A clinical overview photograph of a skin lesion. The chart documents a prior melanoma. A female patient aged 68-72. The patient is skin type II.
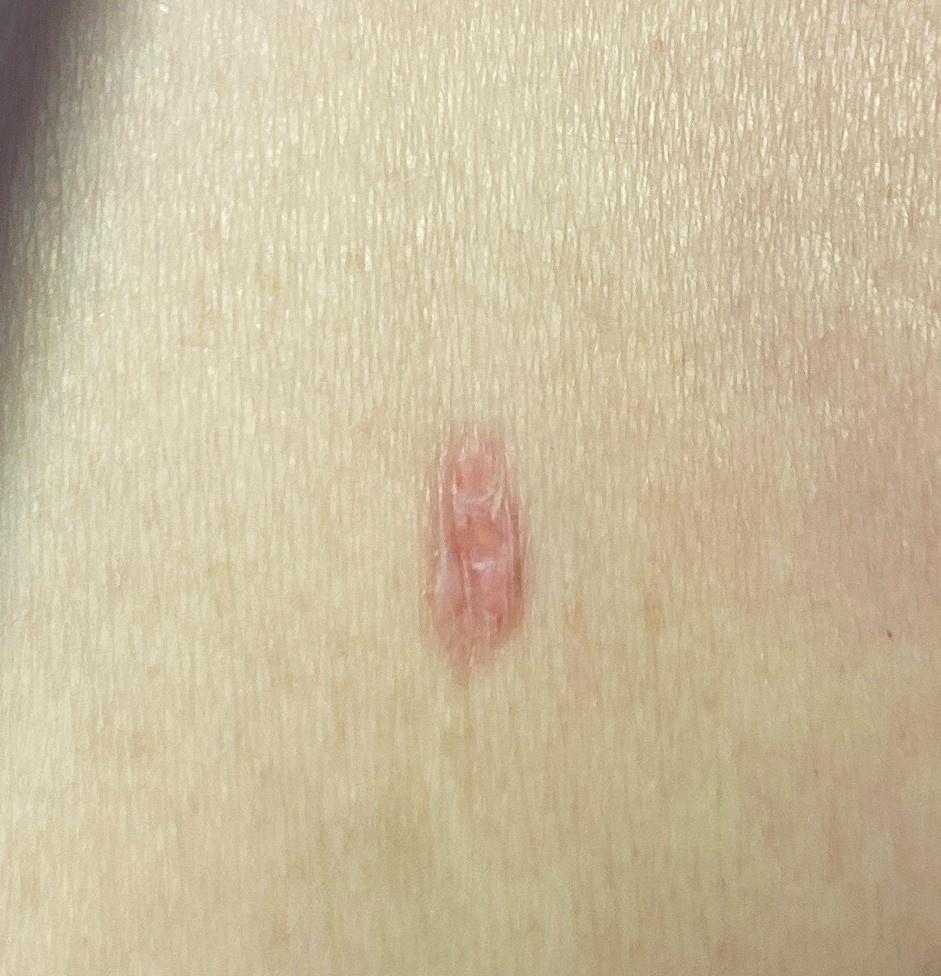The lesion was found on the trunk. On biopsy, the diagnosis was a malignant, adnexal lesion — a basal cell carcinoma.